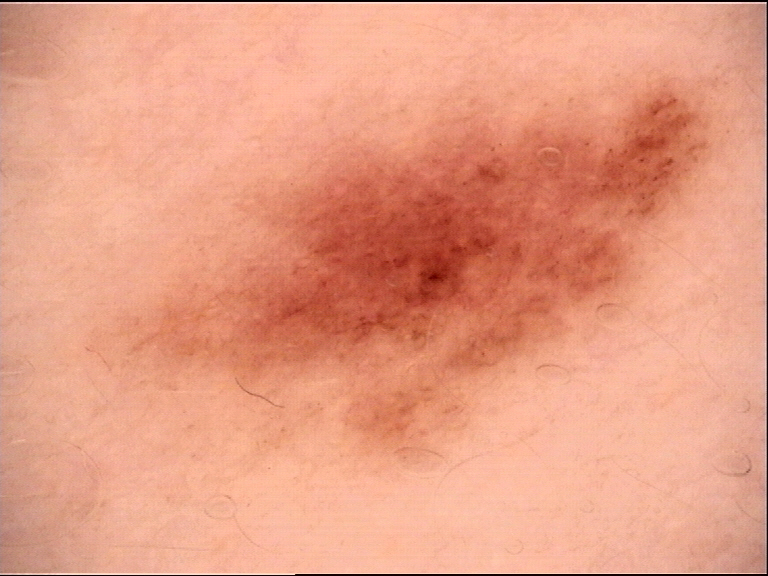Dermoscopy of a skin lesion. Consistent with a dysplastic junctional nevus.